The patient described the issue as a rash, the lesion involves the head or neck and palm, the lesion is described as rough or flaky and raised or bumpy, the photo was captured at an angle, the contributor reports bothersome appearance, reported duration is more than five years, no relevant systemic symptoms:
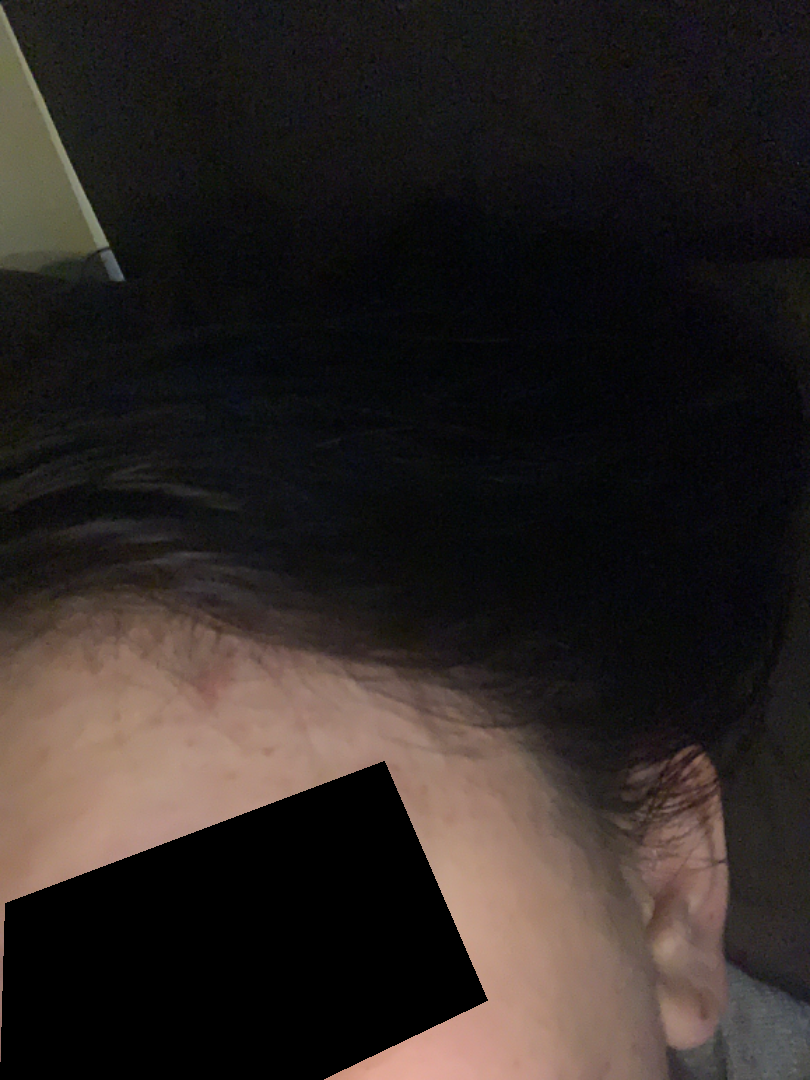The condition could not be reliably identified from the image.